A dermoscopic close-up of a skin lesion.
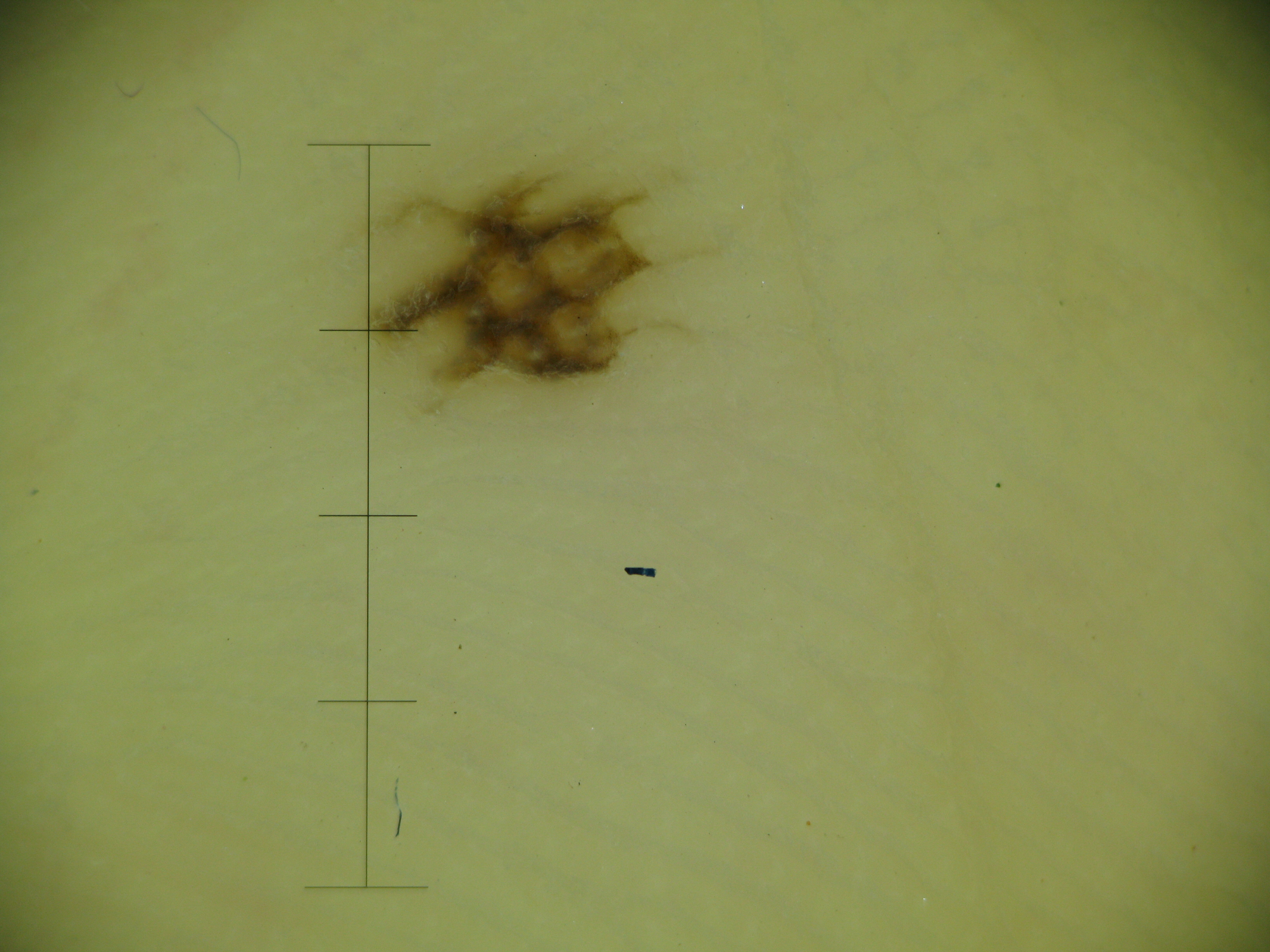category — banal; label — acral junctional nevus (expert consensus).